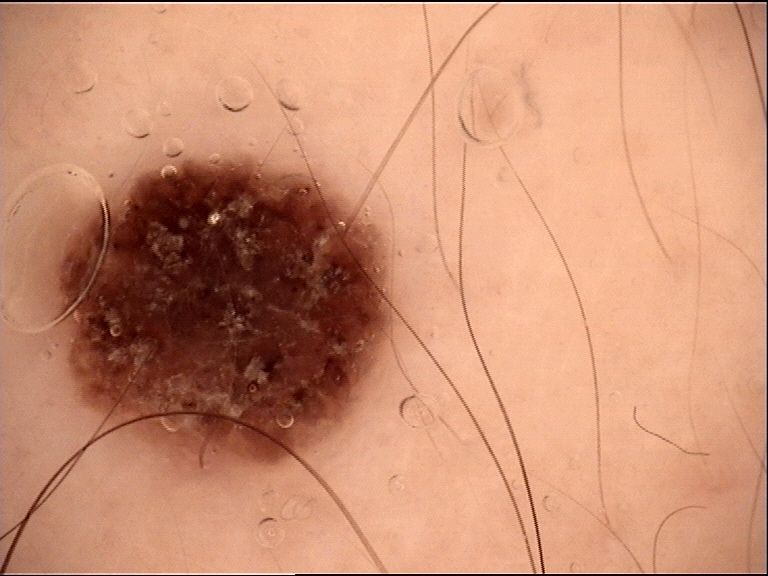Classified as a seborrheic keratosis.